The subject is a female aged 18–29. The photo was captured at a distance. The leg and head or neck are involved — 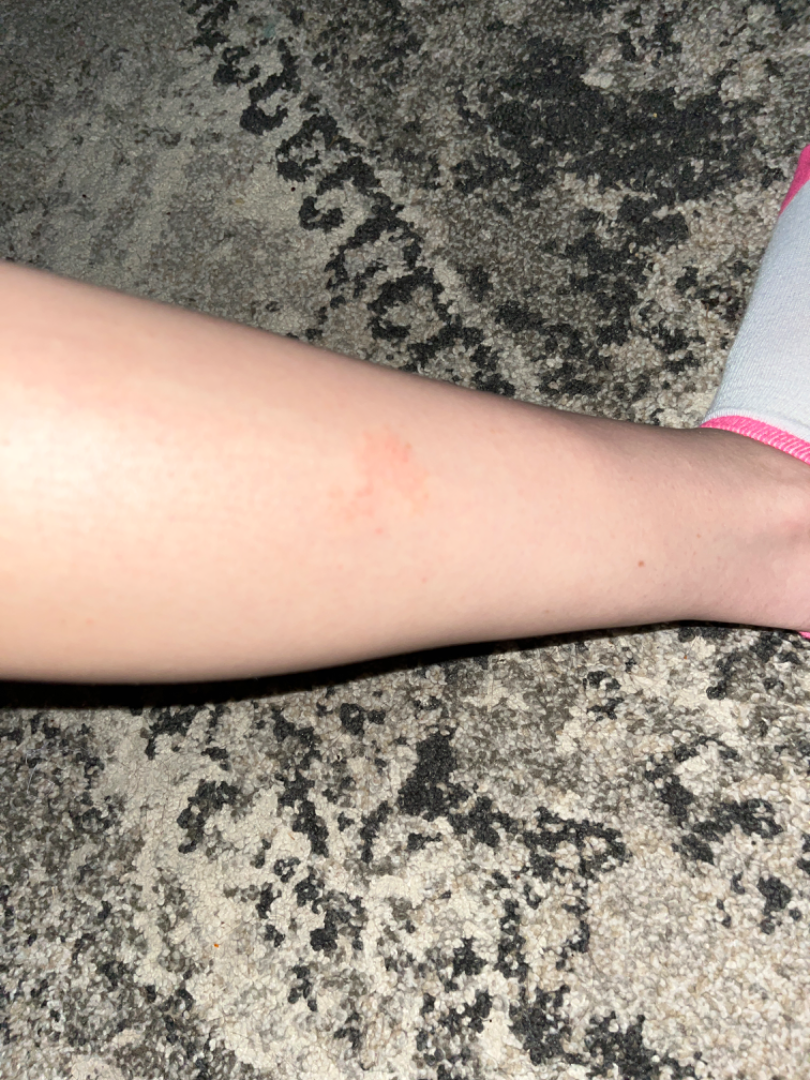Assessment:
On remote review of the image: Xerosis, Eczema and Irritant Contact Dermatitis were considered with similar weight.